A dermoscopic close-up of a skin lesion: 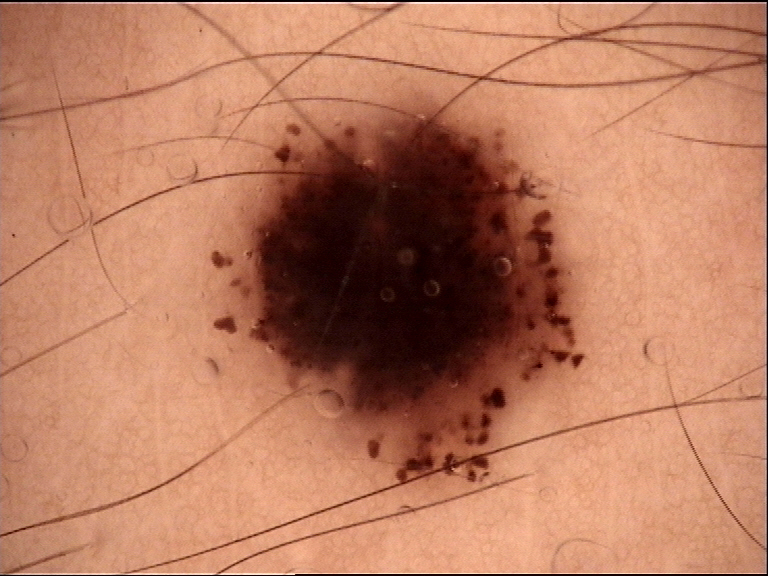{
  "diagnosis": {
    "name": "dysplastic junctional nevus",
    "code": "jd",
    "malignancy": "benign",
    "super_class": "melanocytic",
    "confirmation": "expert consensus"
  }
}